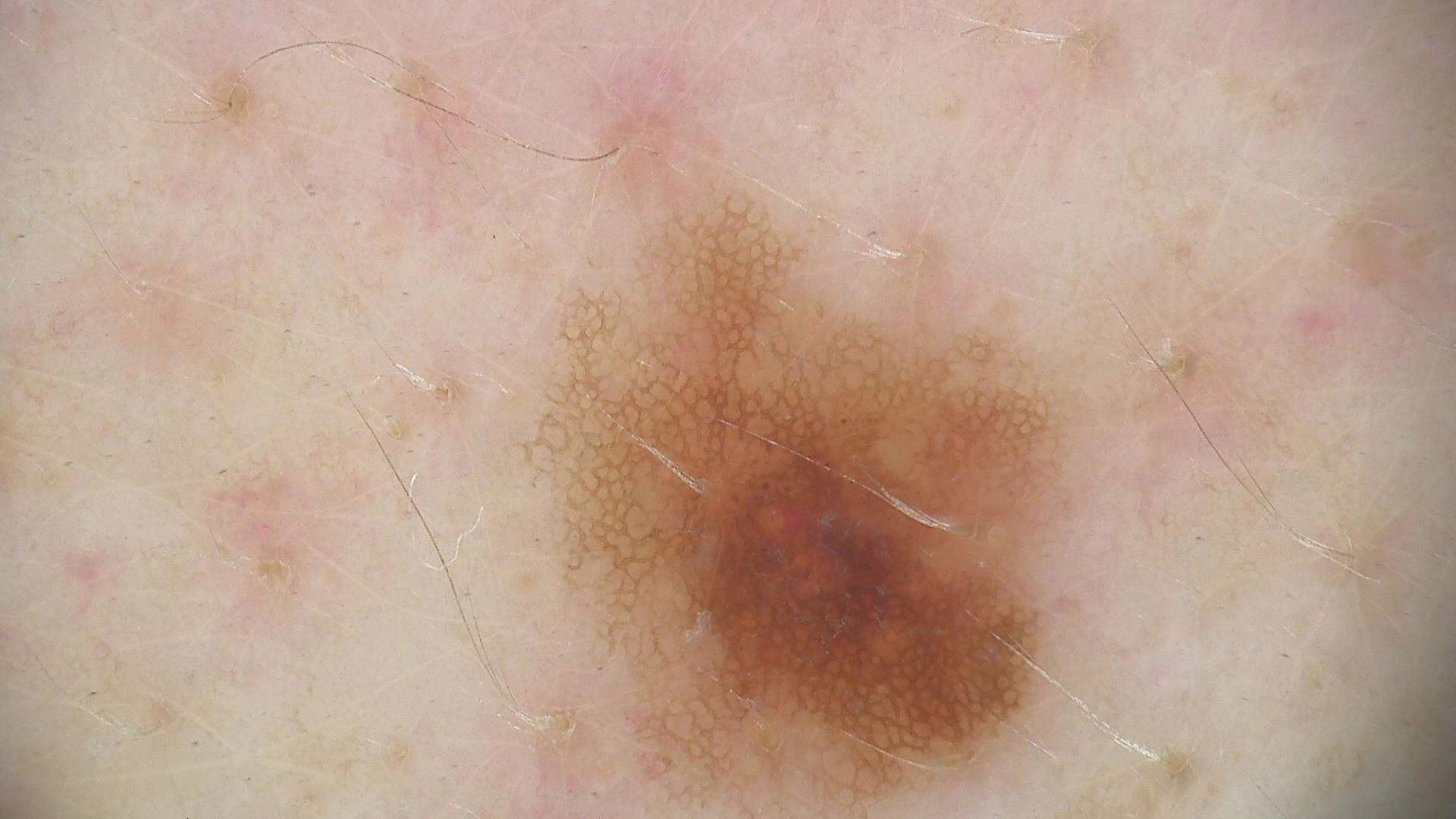{
  "image": "dermoscopy",
  "diagnosis": {
    "name": "dysplastic junctional nevus",
    "code": "jd",
    "malignancy": "benign",
    "super_class": "melanocytic",
    "confirmation": "expert consensus"
  }
}